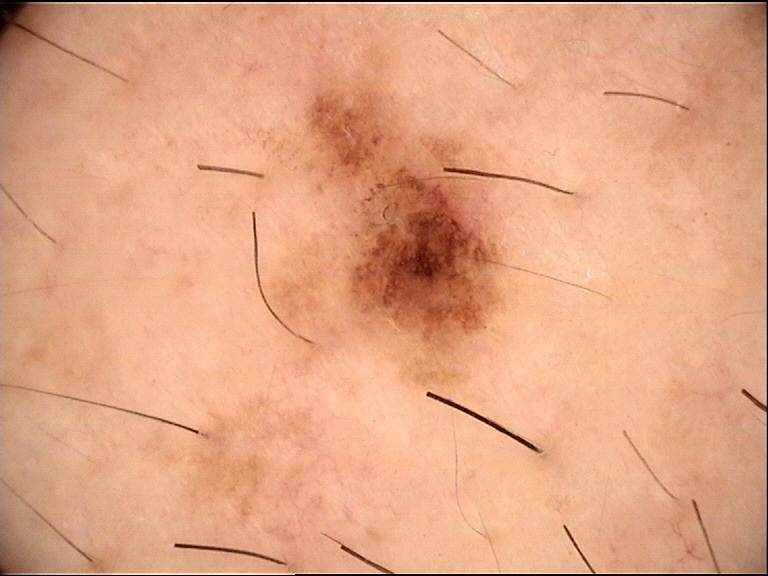Impression:
Diagnosed as a dysplastic junctional nevus.